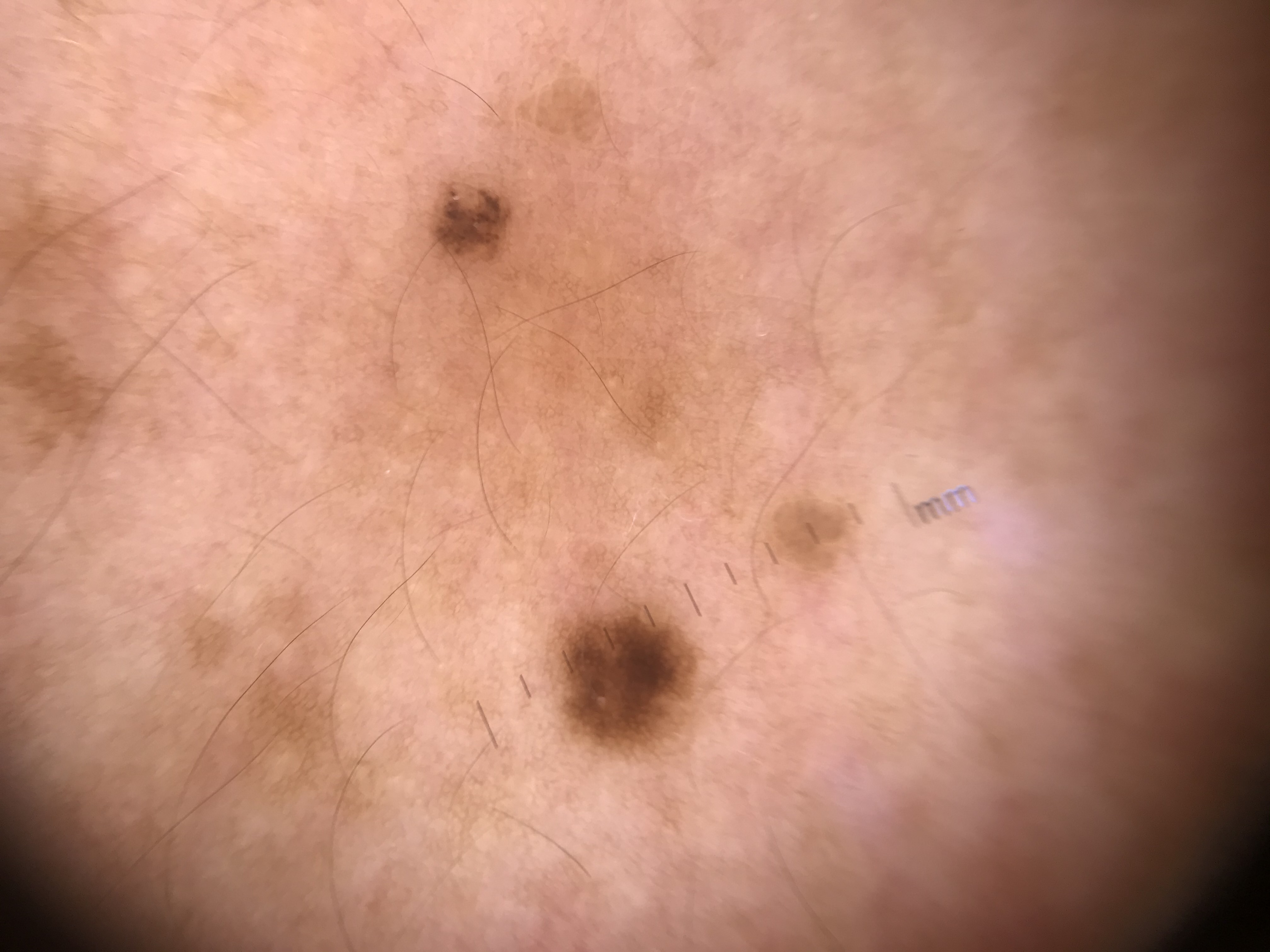diagnosis: junctional nevus (expert consensus).